A dermoscopic photograph of a skin lesion:
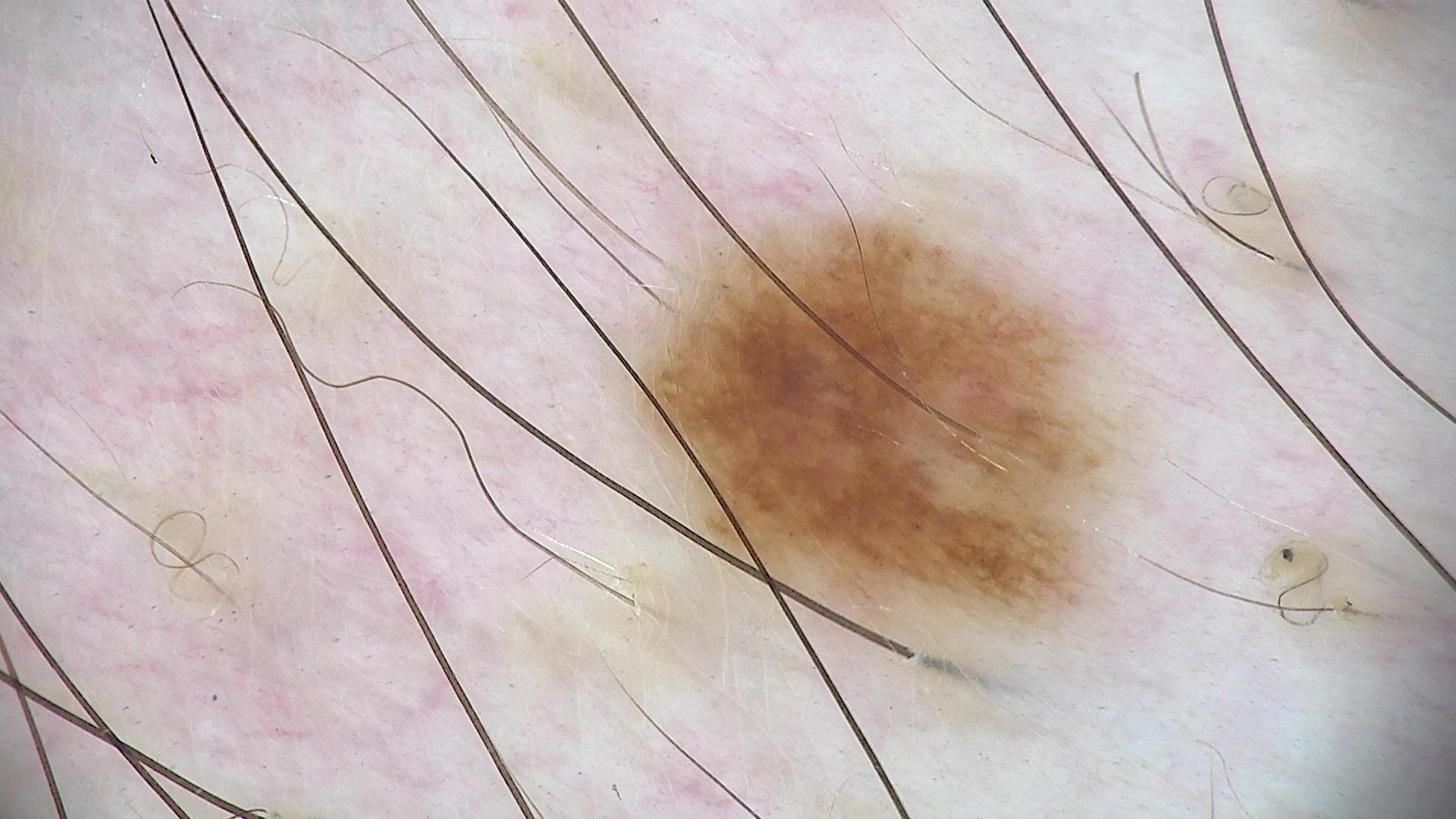  diagnosis:
    name: dysplastic junctional nevus
    code: jd
    malignancy: benign
    super_class: melanocytic
    confirmation: expert consensus